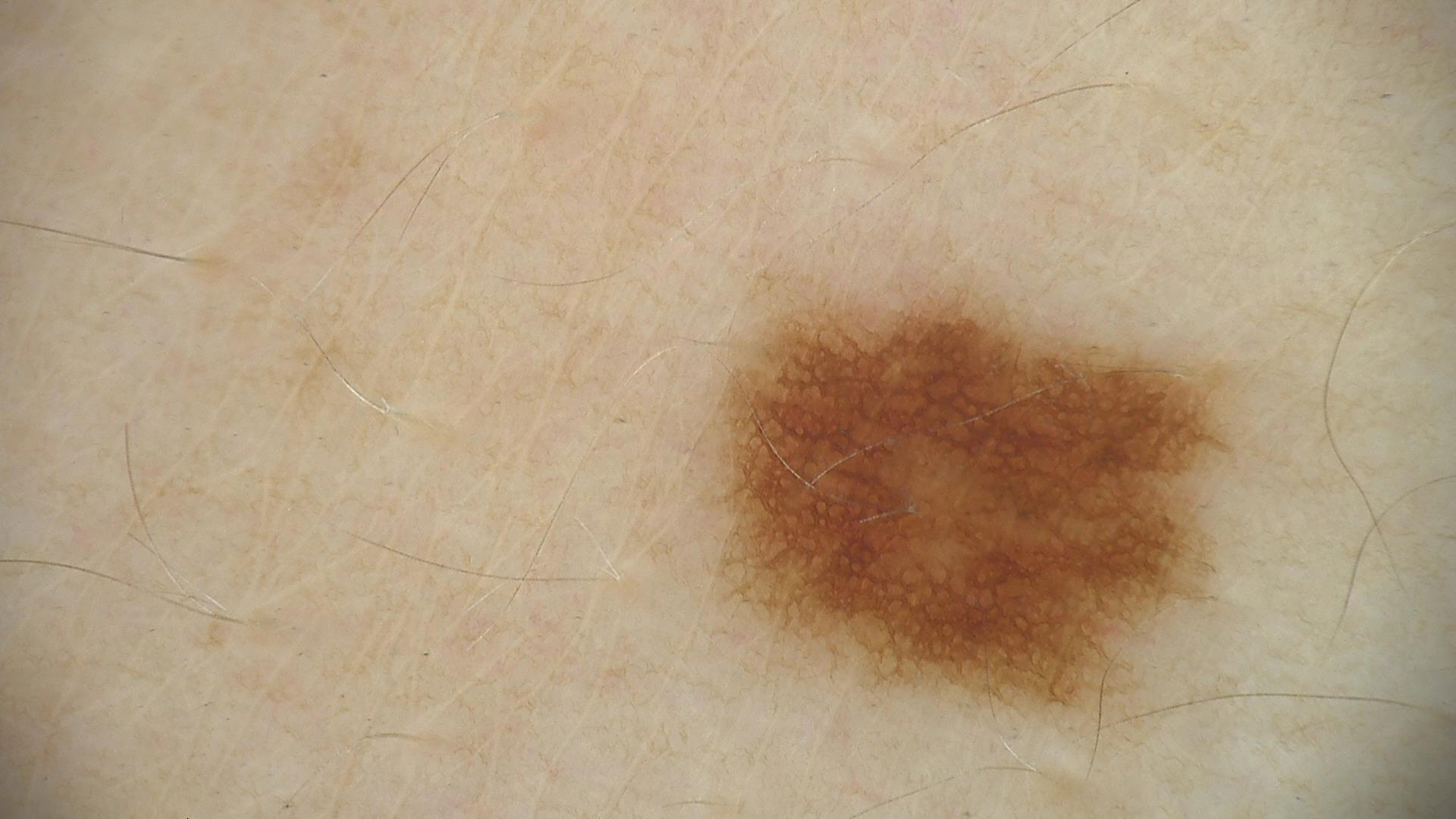{"image": "dermatoscopy", "diagnosis": {"name": "dysplastic junctional nevus", "code": "jd", "malignancy": "benign", "super_class": "melanocytic", "confirmation": "expert consensus"}}